A dermoscopic photograph of a skin lesion.
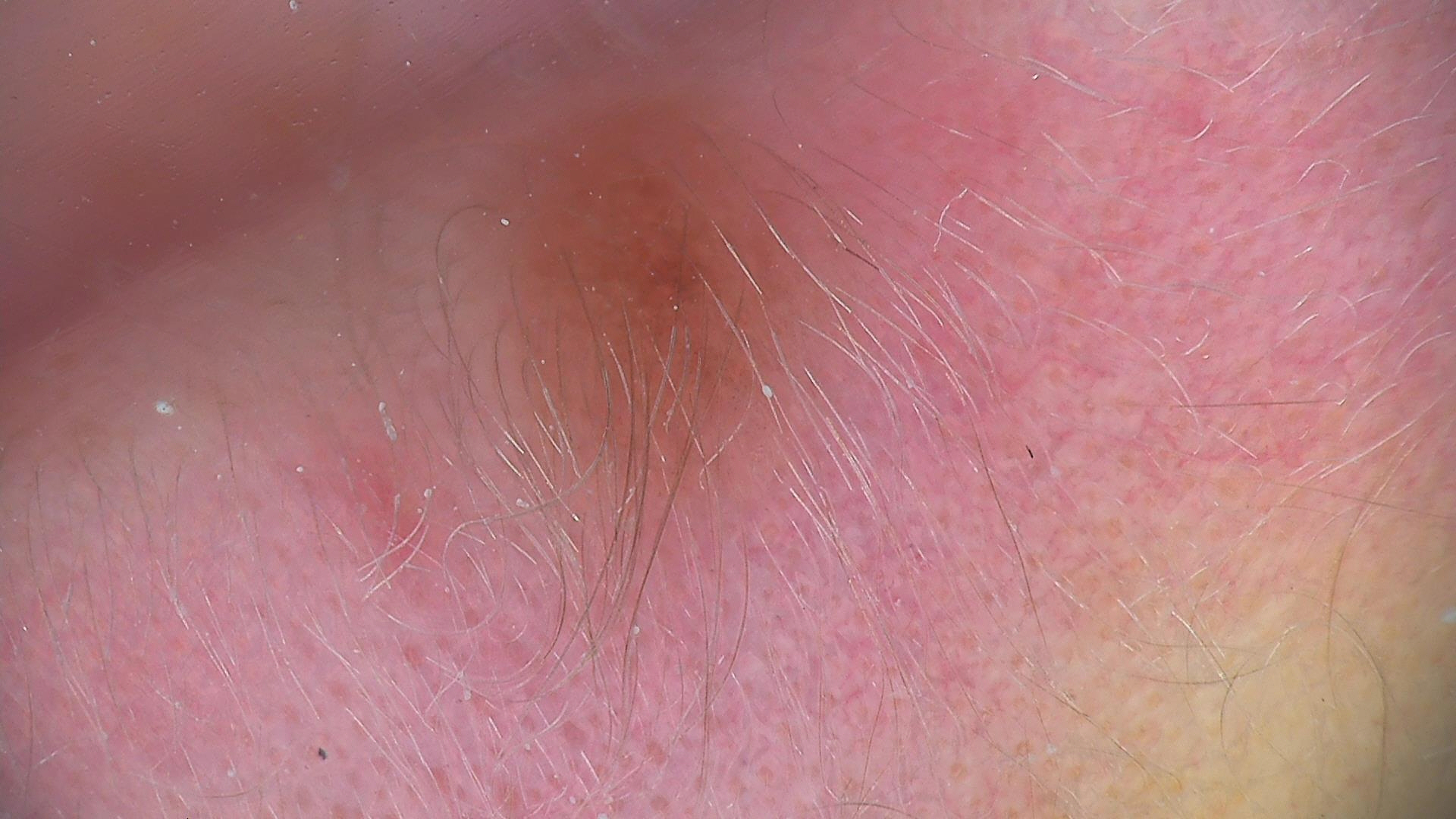assessment = dermal nevus (expert consensus).